The front of the torso, head or neck and back of the torso are involved · this is a close-up image — 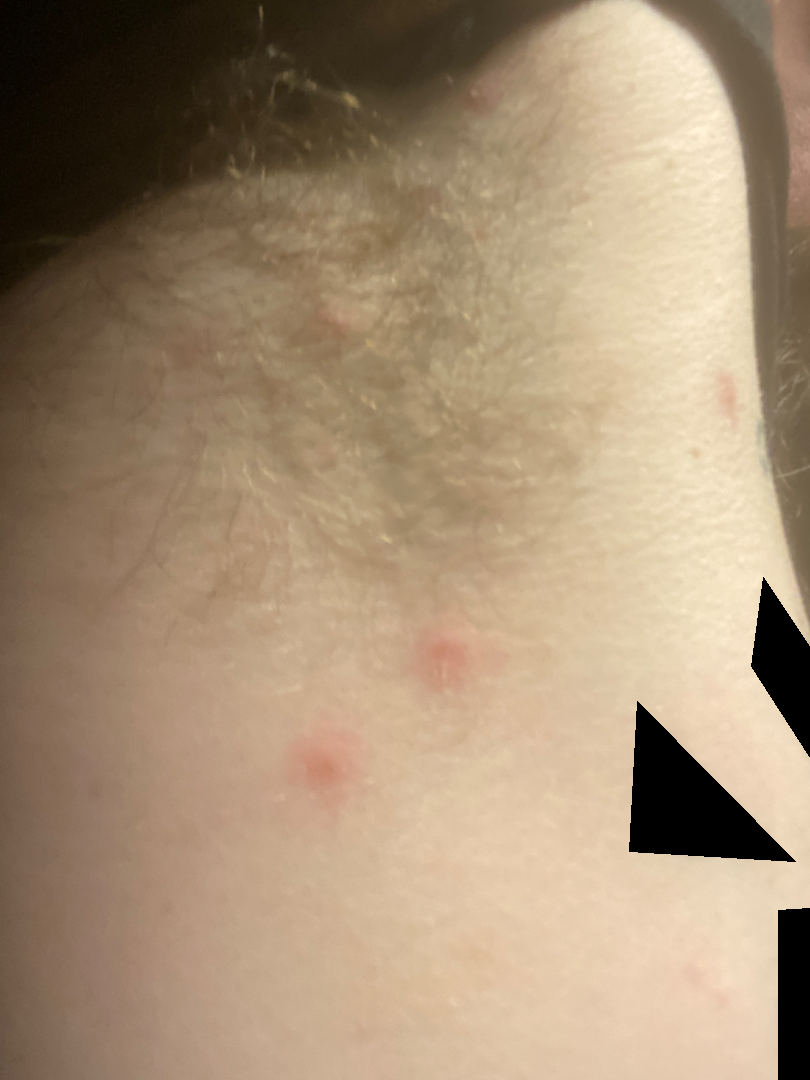Findings: On remote dermatologist review: favoring Folliculitis.